A dermoscopic close-up of a skin lesion: 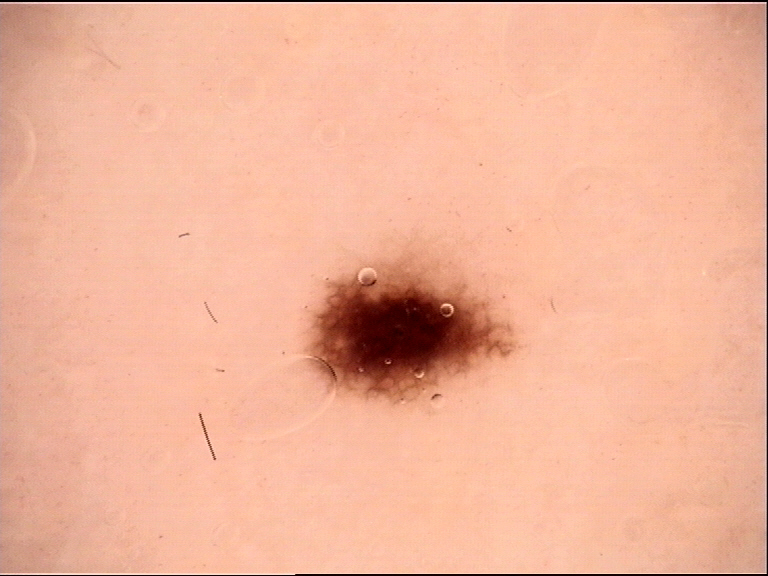Diagnosed as a dysplastic junctional nevus.